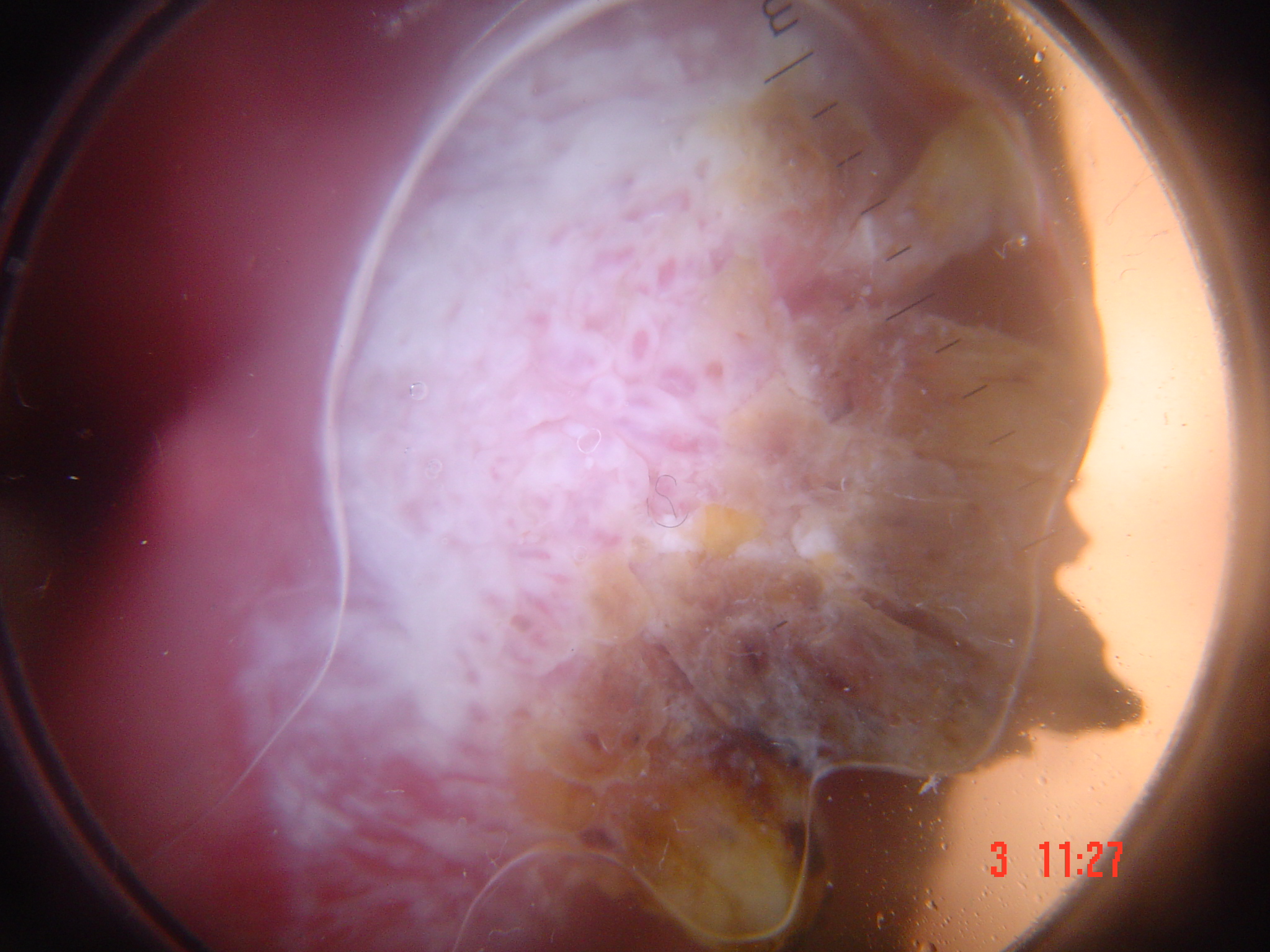modality — dermatoscopy; classification — keratinocytic; class — squamous cell carcinoma (biopsy-proven).